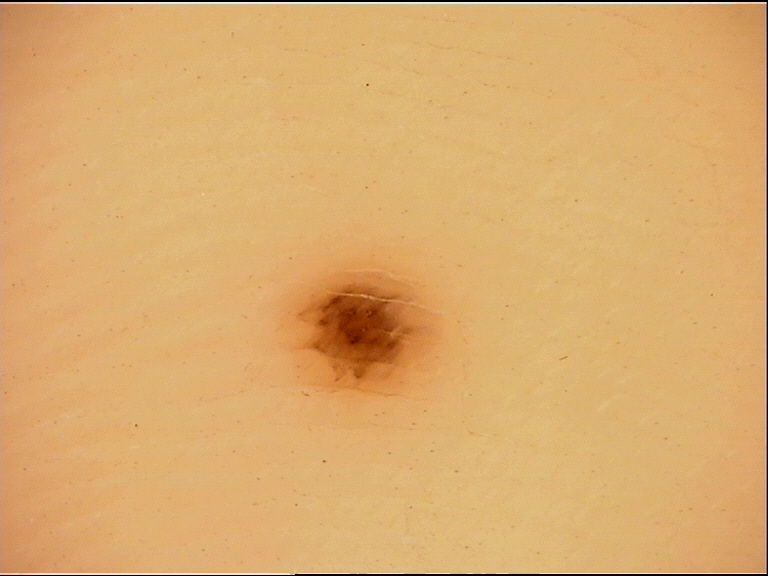Dermoscopy of a skin lesion.
The morphology is that of a banal lesion.
Consistent with an acral junctional nevus.